The head or neck is involved, the photograph was taken at a distance.
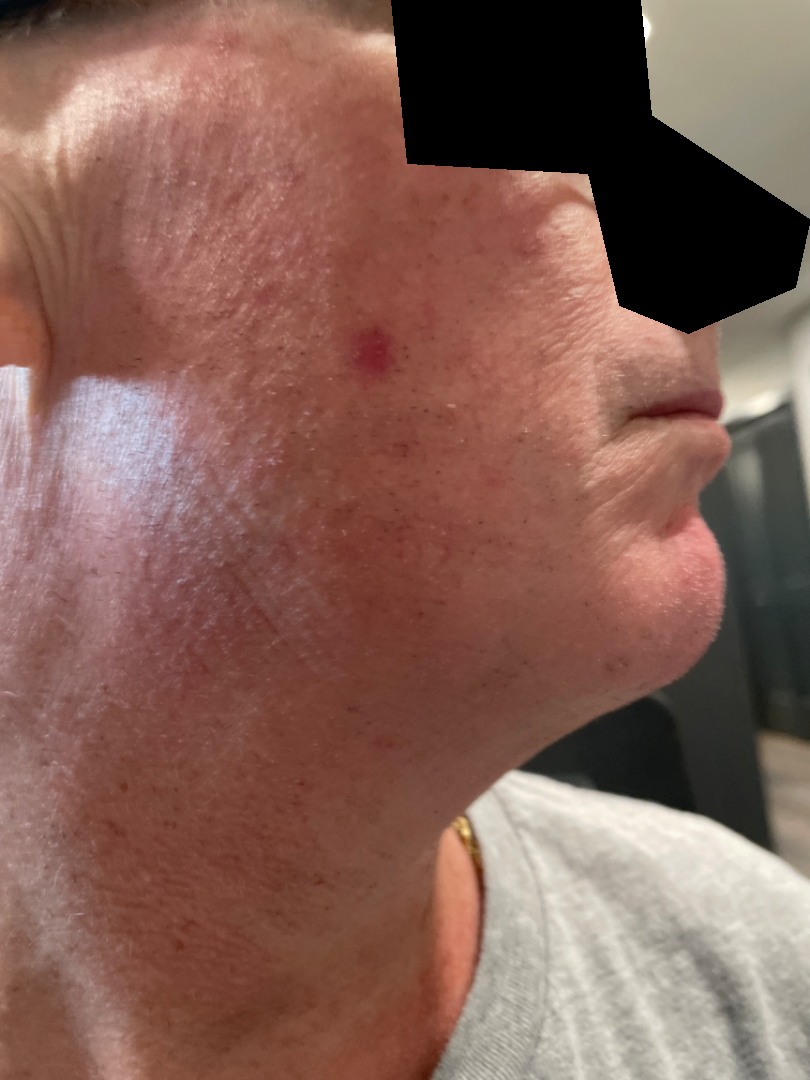assessment: indeterminate from the photograph
systemic_symptoms: none reported
duration: one to three months
symptoms: itching
texture: flat